A patient in their 70s. A clinical photograph showing a skin lesion.
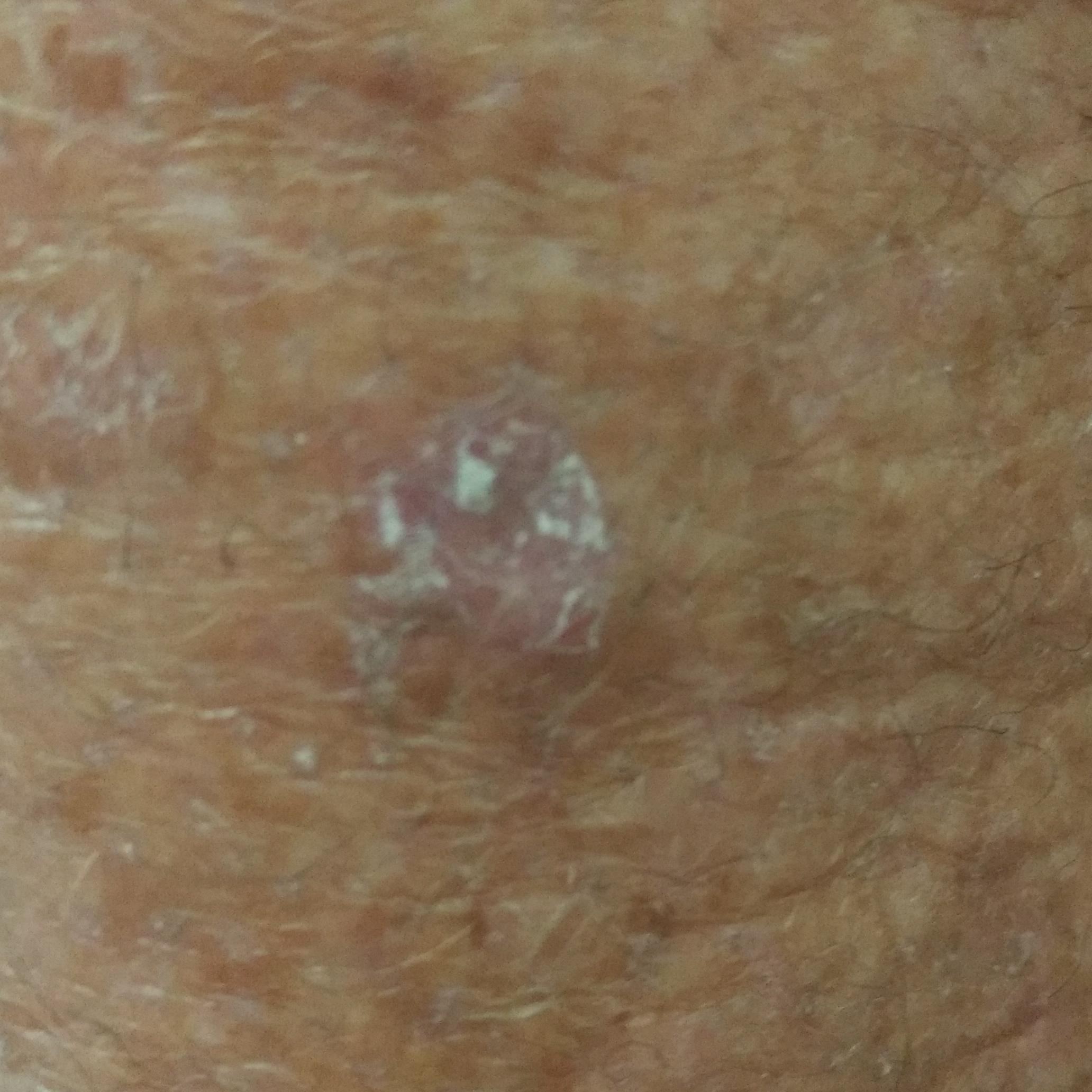Q: What is the anatomic site?
A: a thigh
Q: What symptoms does the patient report?
A: itching / no growth, no bleeding
Q: What is this lesion?
A: actinic keratosis (clinical consensus)